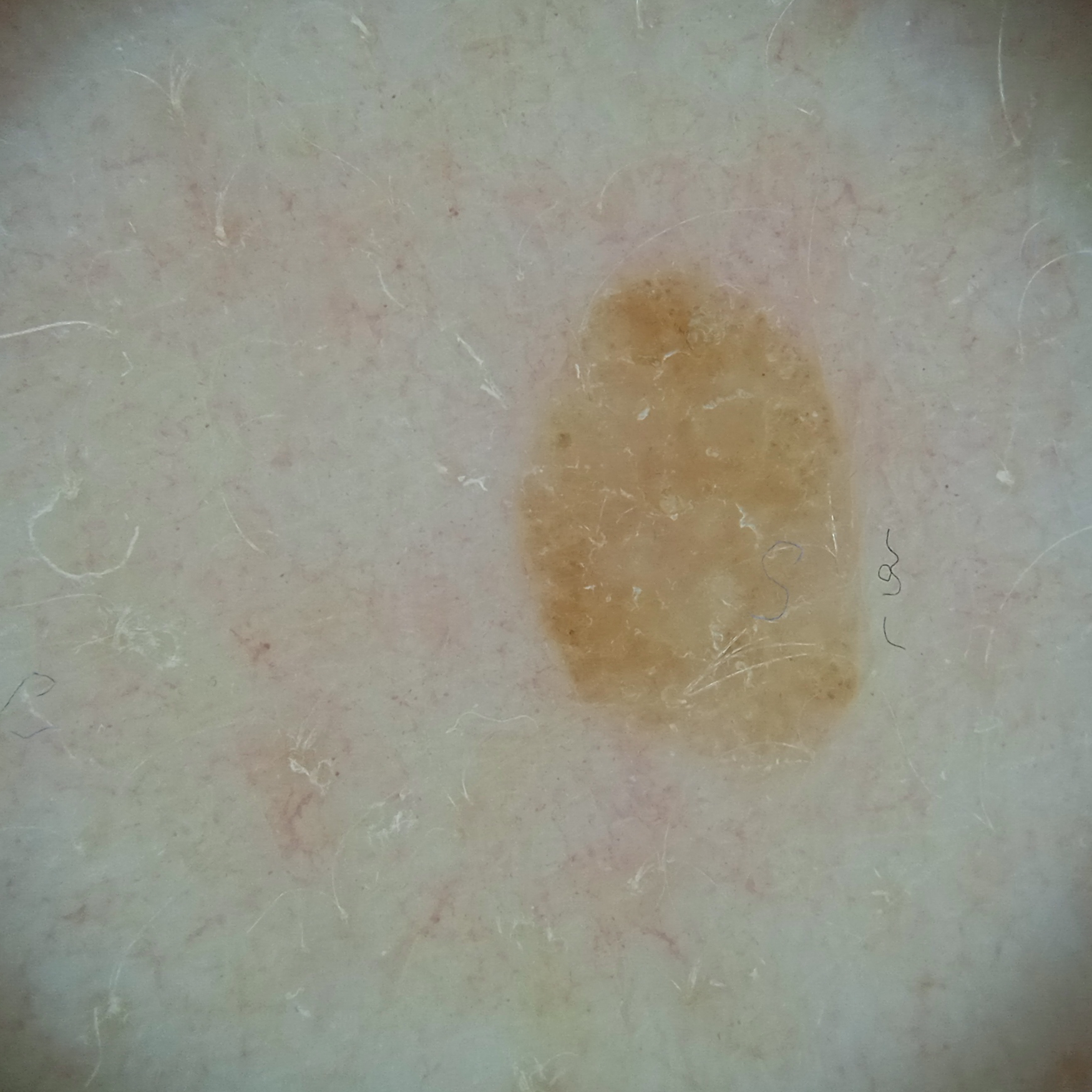The patient describes having numerous moles. Acquired for a research image collection, with no referral diagnosis. A dermoscopic image of a skin lesion. A female subject 54 years of age. Measuring roughly 5.5 mm. Four dermatologists reviewed the lesion; the consensus was a seborrheic keratosis; agreement among the reviewers was unanimous; diagnostic confidence was good.